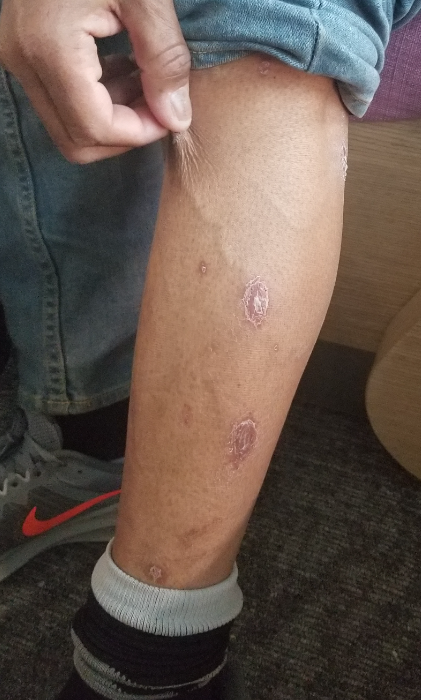differential diagnosis — Psoriasis (0.61); Eczema (0.22); Syphilis (0.17).